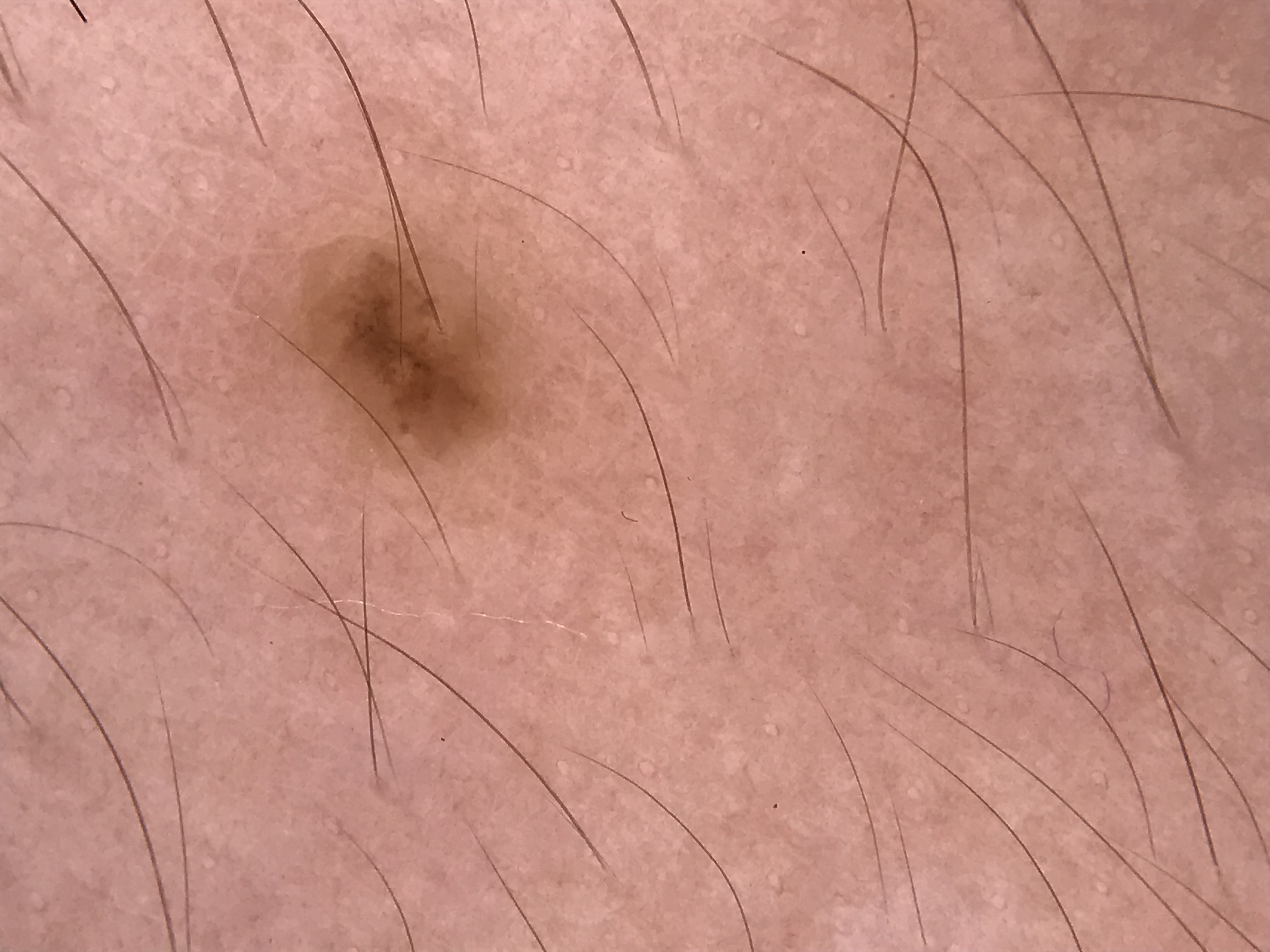modality = dermoscopy, assessment = junctional nevus (expert consensus).